The photograph is a close-up of the affected area; the lesion involves the back of the hand, arm and head or neck; the contributor is 40–49, male: 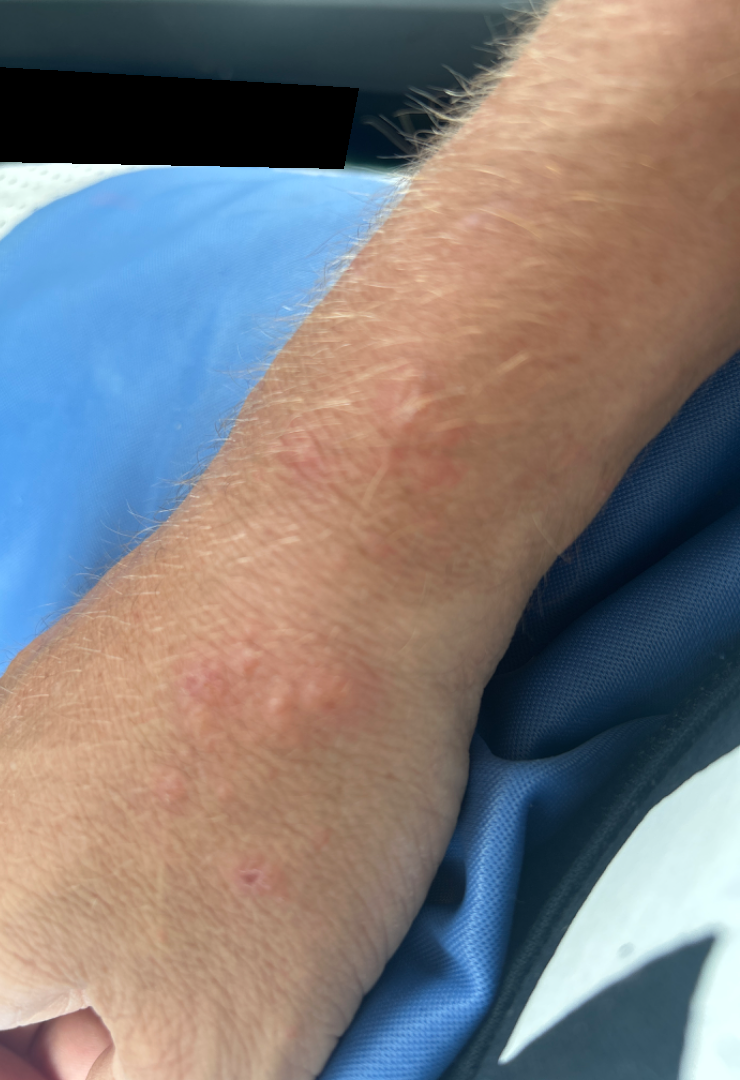Deep fungal infection (primary).